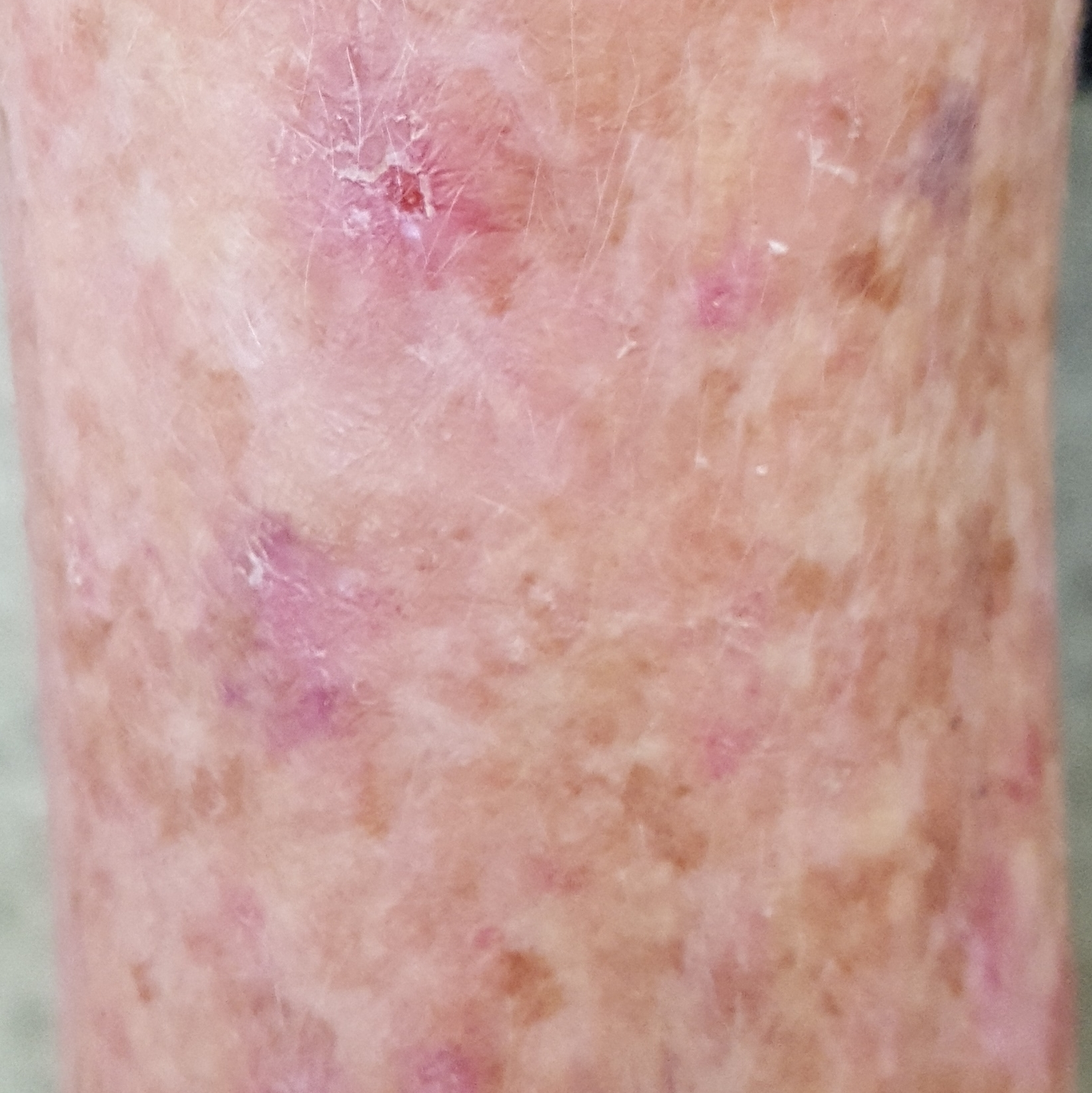patient = aged 70 | modality = clinical photograph | site = a forearm | reported symptoms = itching | diagnostic label = actinic keratosis (clinical consensus).